A dermoscopy image of a single skin lesion: 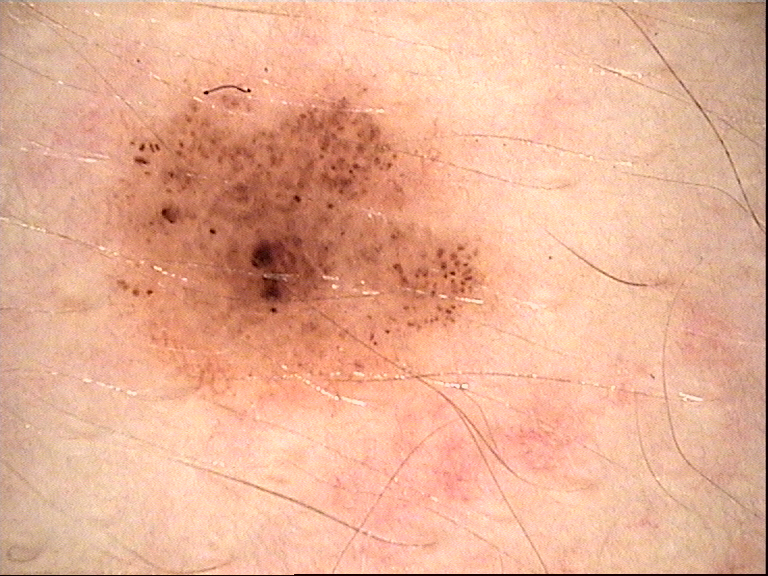Classified as a dysplastic junctional nevus.